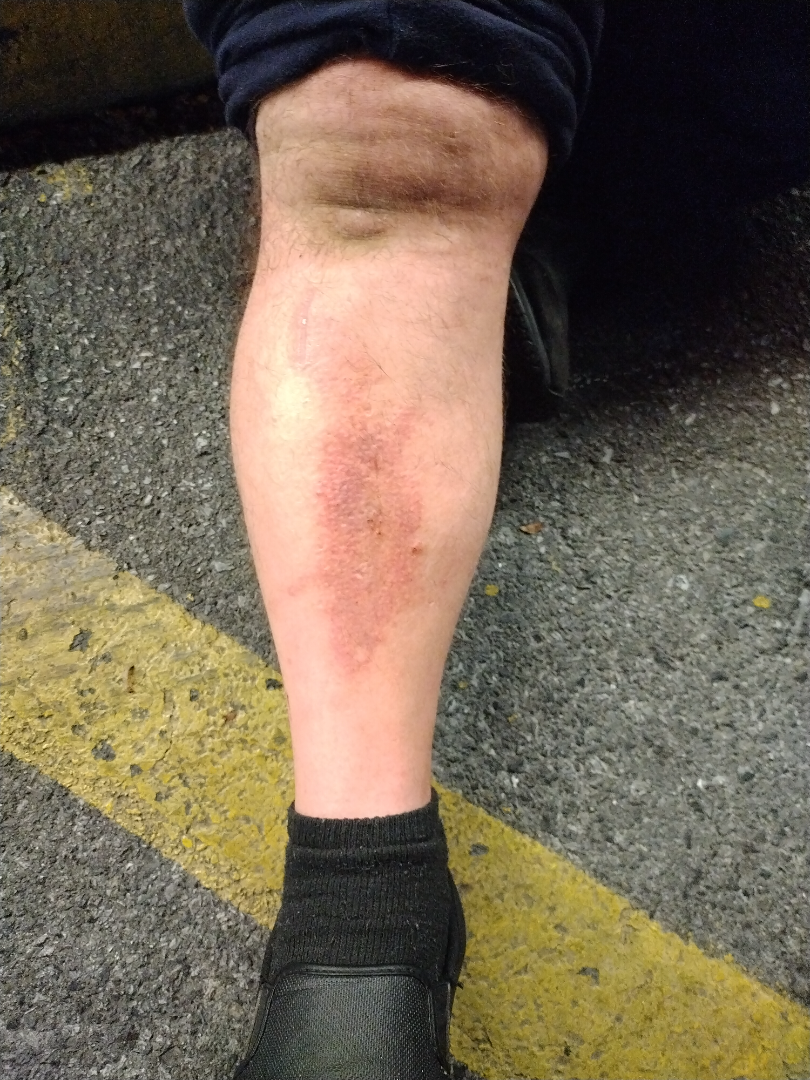Allergic Contact Dermatitis (leading); Eczema (possible); Amyloidosis of skin (possible).